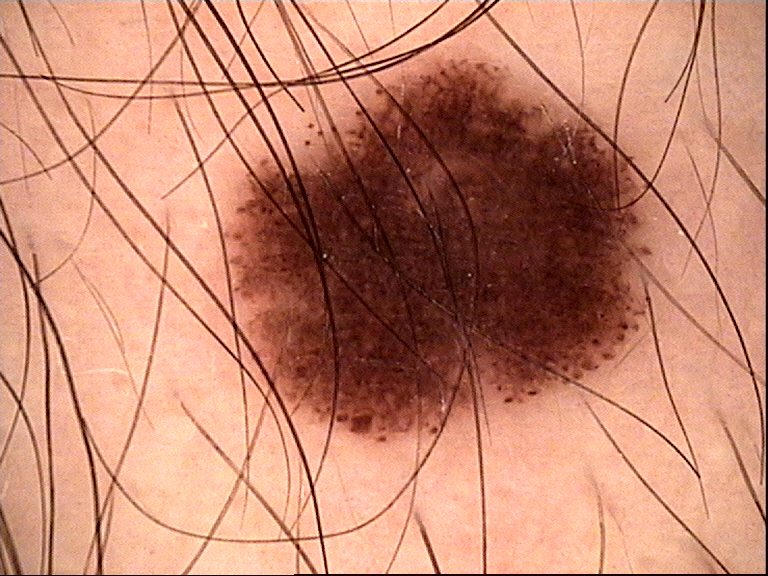Labeled as a dysplastic junctional nevus.